The photograph was taken at an angle.
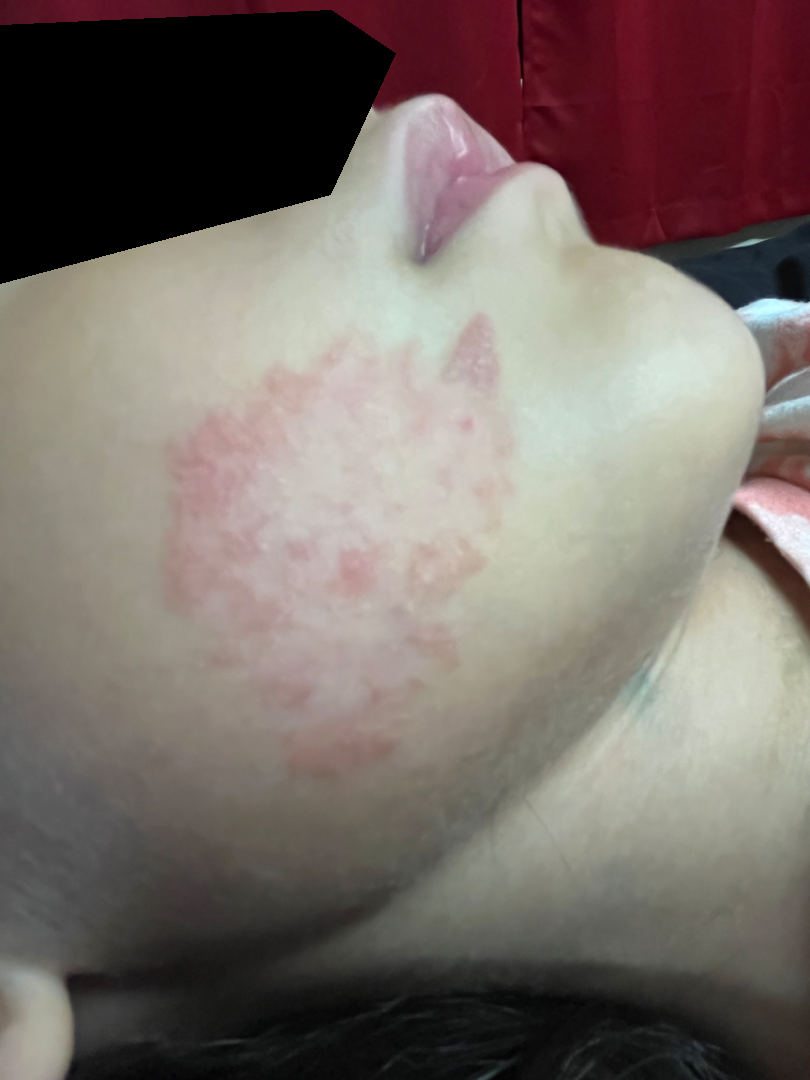On photographic review by a dermatologist, Hemangioma (leading); Granuloma faciale (considered).